A dermoscopic view of a skin lesion: 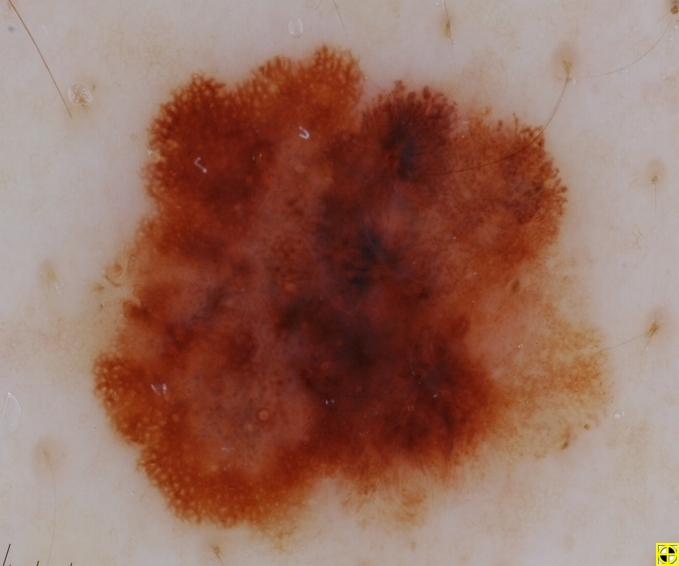lesion_location:
  bbox_xyxy:
    - 48
    - 39
    - 609
    - 561
dermoscopic_features:
  present:
    - streaks
    - globules
    - pigment network
    - negative network
  absent:
    - milia-like cysts
lesion_extent:
  approx_field_fraction_pct: 54
diagnosis:
  name: melanoma
  malignancy: malignant
  lineage: melanocytic
  provenance: histopathology